Reported duration is less than one week. Skin tone: Fitzpatrick skin type IV; human graders estimated a Monk Skin Tone of 4. The photograph is a close-up of the affected area. The patient notes the lesion is raised or bumpy. The affected area is the leg:
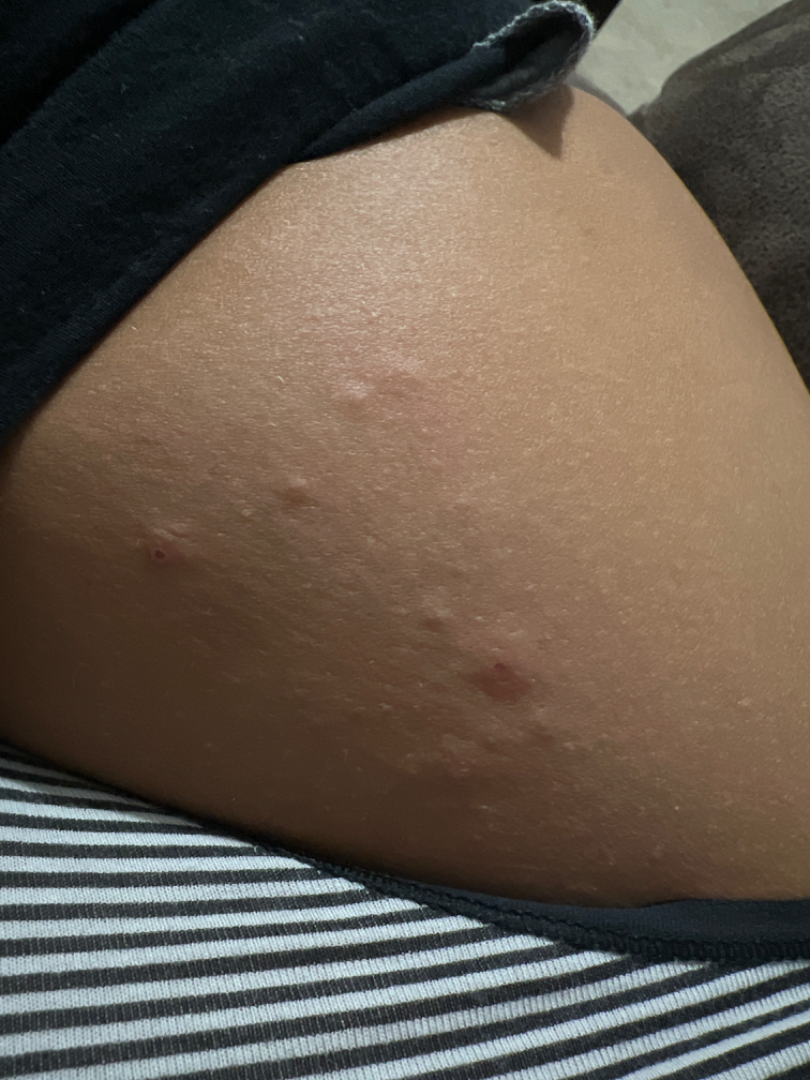Assessment: Reviewed remotely by one dermatologist: Impetigo, Insect Bite and Herpes Simplex were each considered, in no particular order.